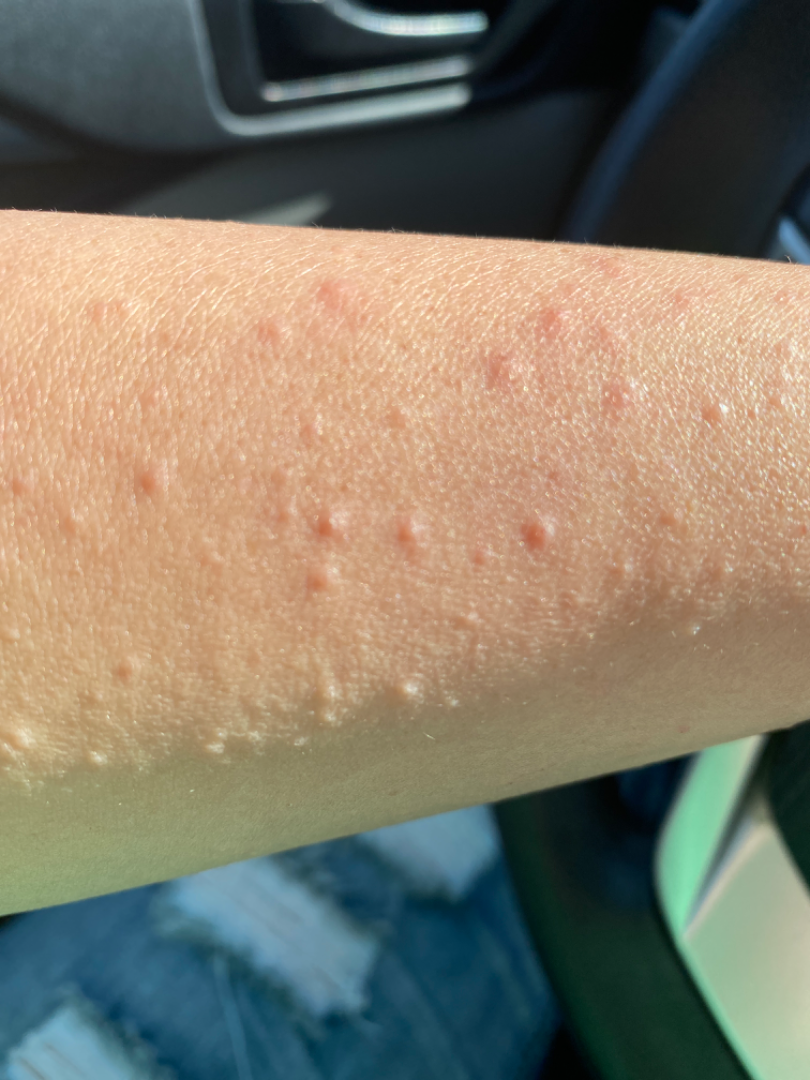history: less than one week; surface texture: raised or bumpy; subject: female; patient-reported symptoms: itching; body site: arm and leg; constitutional symptoms: none reported; framing: close-up; dermatologist impression: Eczema, Viral dermatological disorders and Hypersensitivity were each considered, in no particular order.